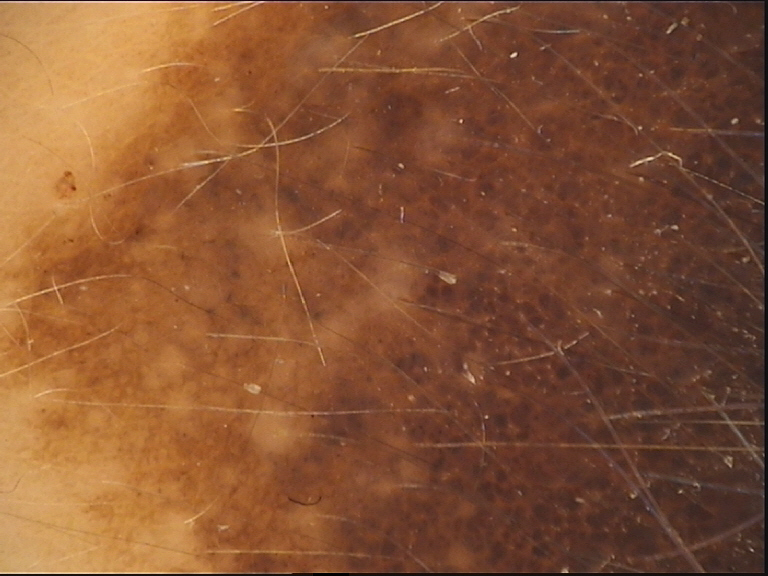The morphology is that of a banal lesion. The diagnosis was a congenital compound nevus.